A dermoscopic photograph of a skin lesion.
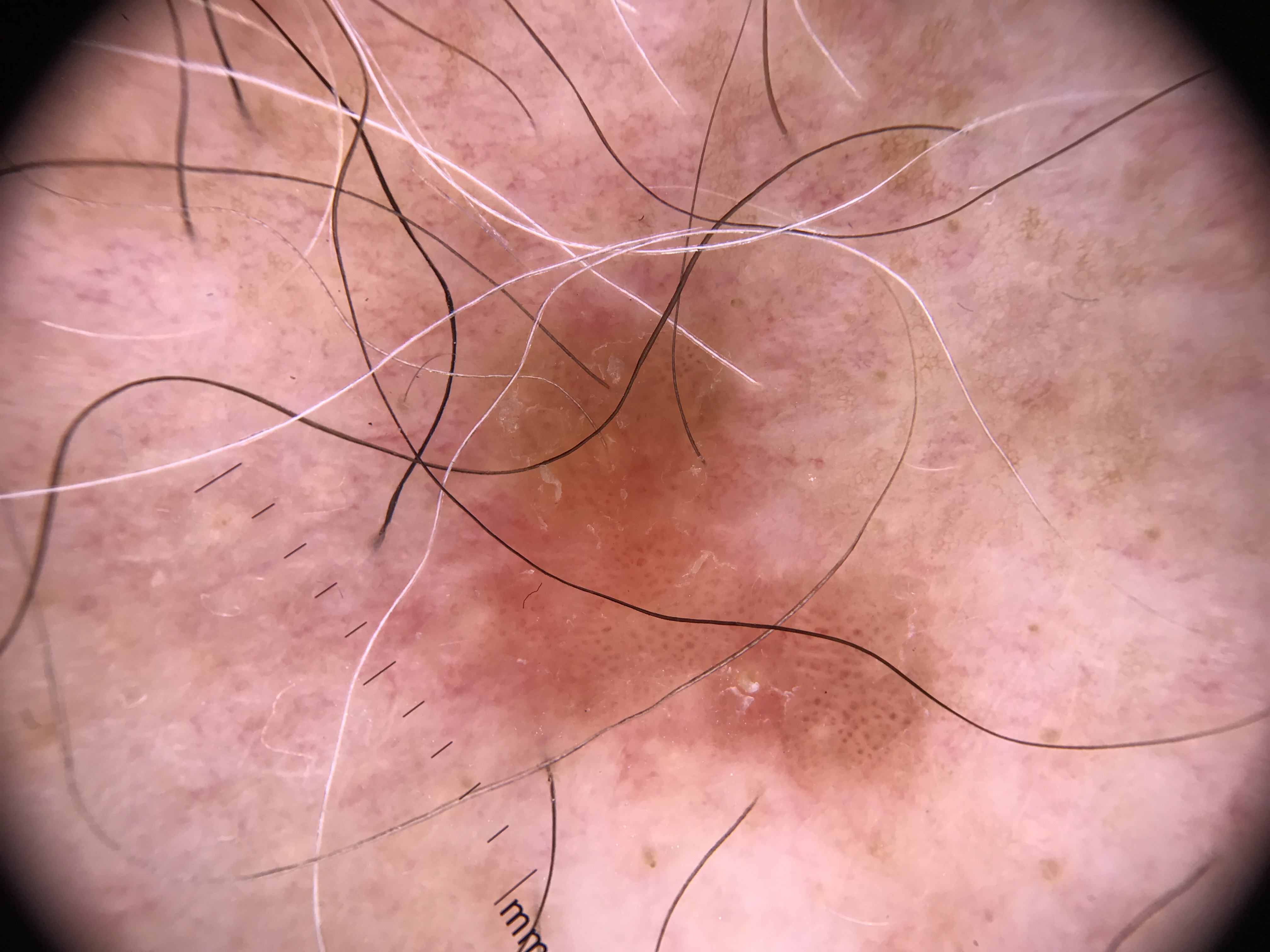The morphology is that of a keratinocytic lesion.
Confirmed on histopathology as a malignant lesion — a basal cell carcinoma.